The patient notes enlargement, skin tone: Fitzpatrick III; lay graders estimated a MST of 2, the sole of the foot and top or side of the foot are involved, no constitutional symptoms were reported, an image taken at an angle, the lesion is described as raised or bumpy, the condition has been present for more than one year, the patient considered this a rash, the subject is a male aged 18–29: 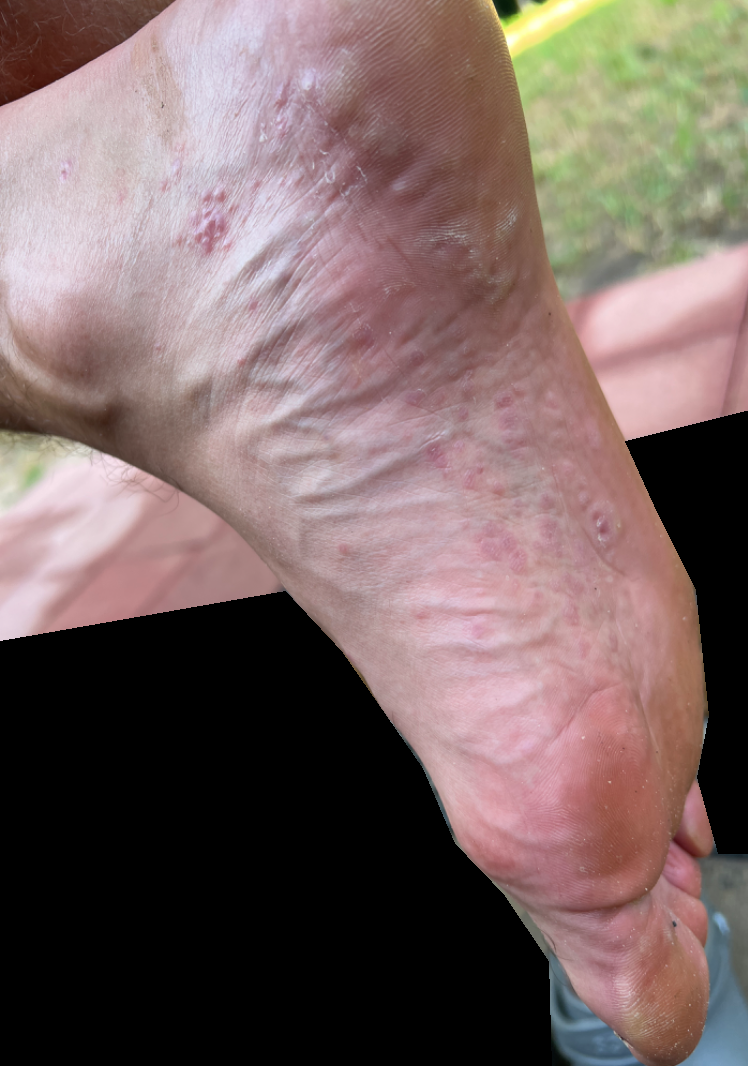  differential:
    leading:
      - Lichen planus/lichenoid eruption
    considered:
      - Insect Bite
      - Allergic Contact Dermatitis